A dermoscopic image of a skin lesion: 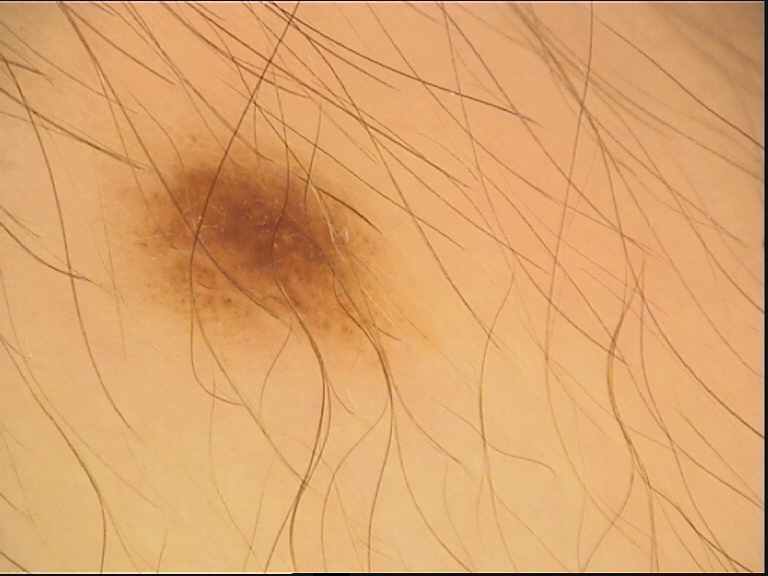Consistent with a benign lesion — a dysplastic junctional nevus.